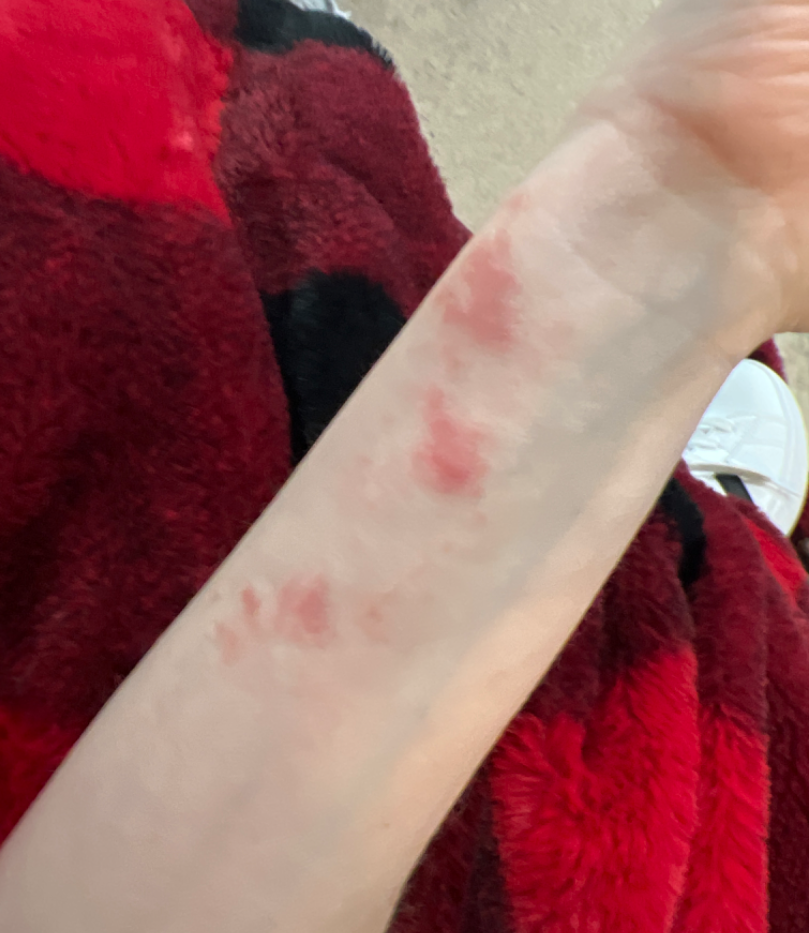Clinical context:
The patient is a female aged 40–49. The photograph was taken at an angle. Located on the arm.
Assessment:
Allergic Contact Dermatitis (favored); Insect Bite (considered); Phytophotodermatitis (remote); Eczema (remote).